Located on the head or neck, a close-up photograph: 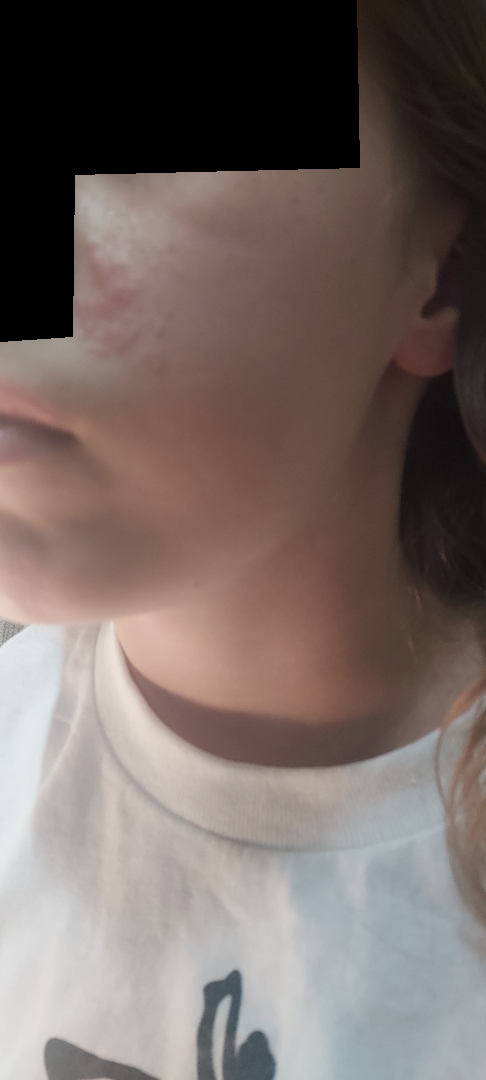{
  "assessment": "could not be assessed",
  "symptoms": "pain",
  "systemic_symptoms": "none reported",
  "patient_category": "skin that appeared healthy to them",
  "texture": [
    "raised or bumpy",
    "rough or flaky"
  ],
  "duration": "one to four weeks"
}